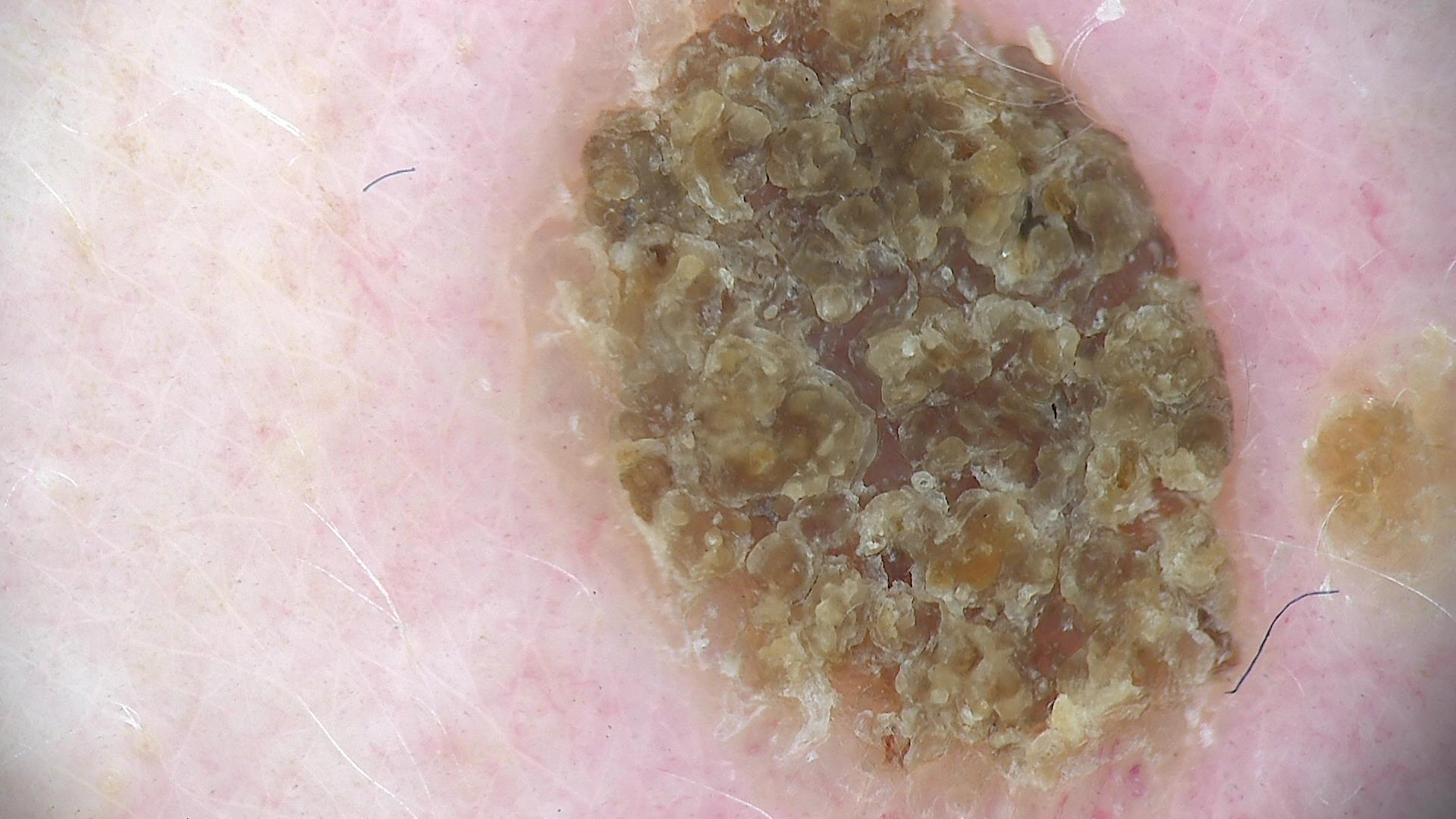assessment=seborrheic keratosis (expert consensus).